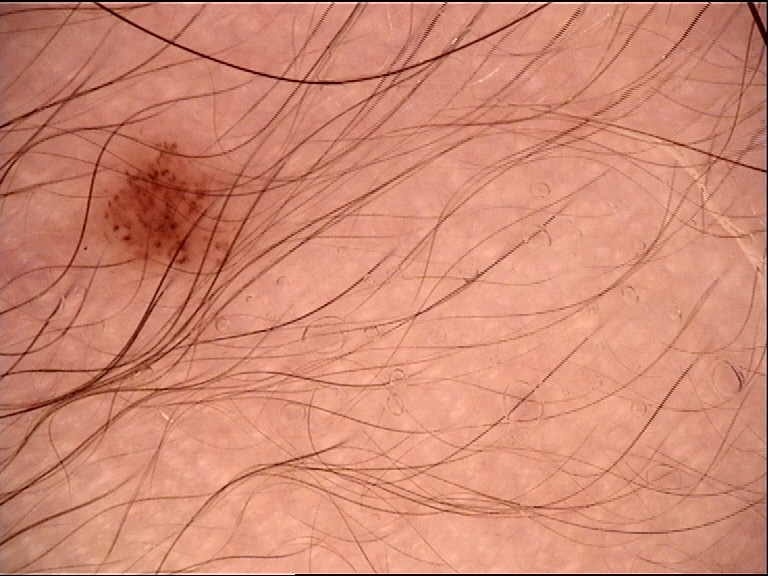The diagnosis was a dysplastic junctional nevus.